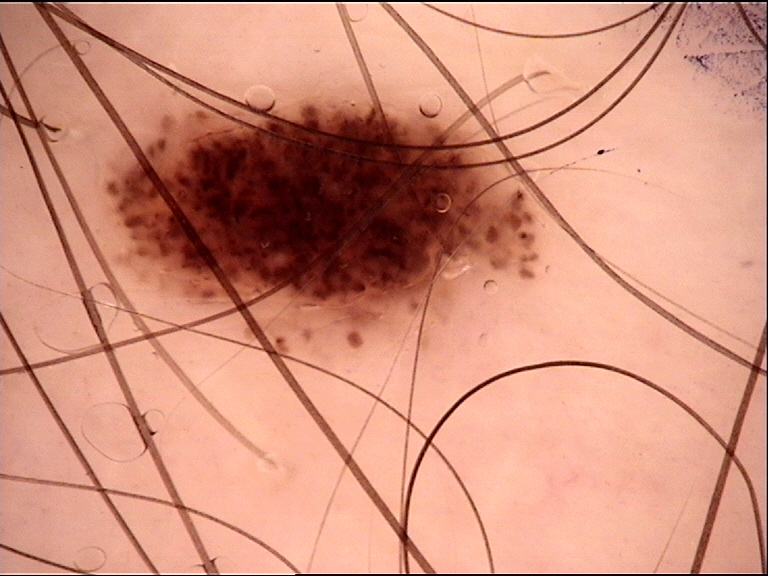The diagnosis was a dysplastic junctional nevus.